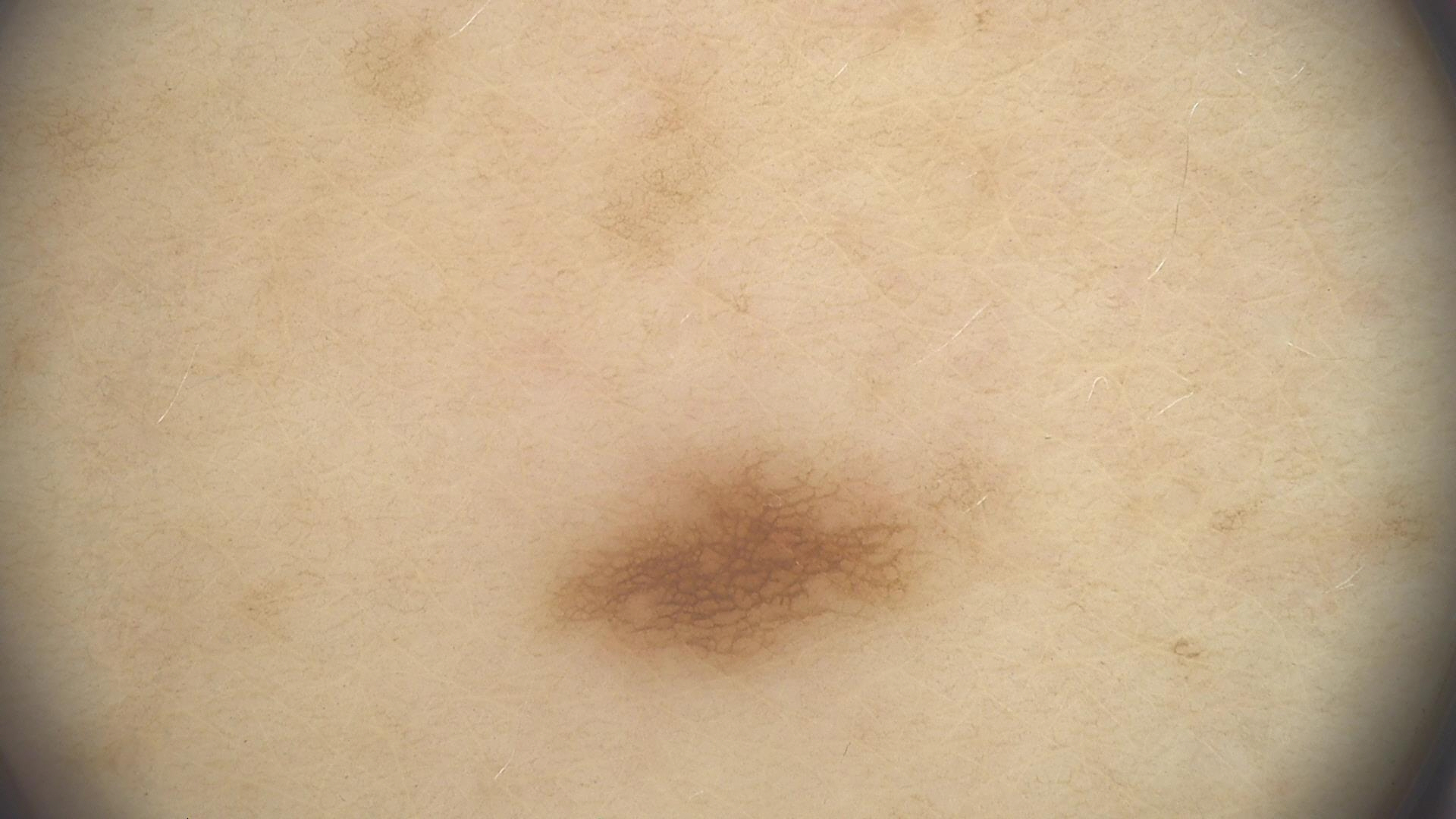modality — dermoscopy
category — banal
label — junctional nevus (expert consensus)